A dermatoscopic image of a skin lesion.
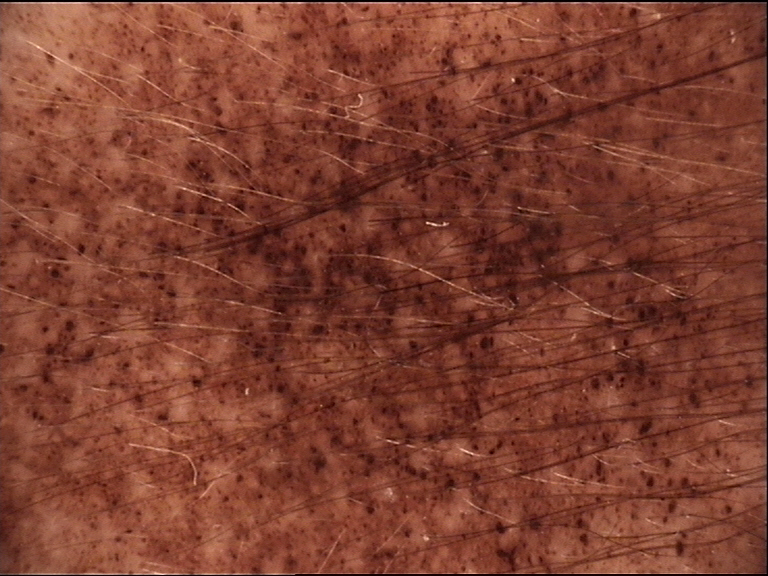assessment = congenital compound nevus (expert consensus)